A dermatoscopic image of a skin lesion:
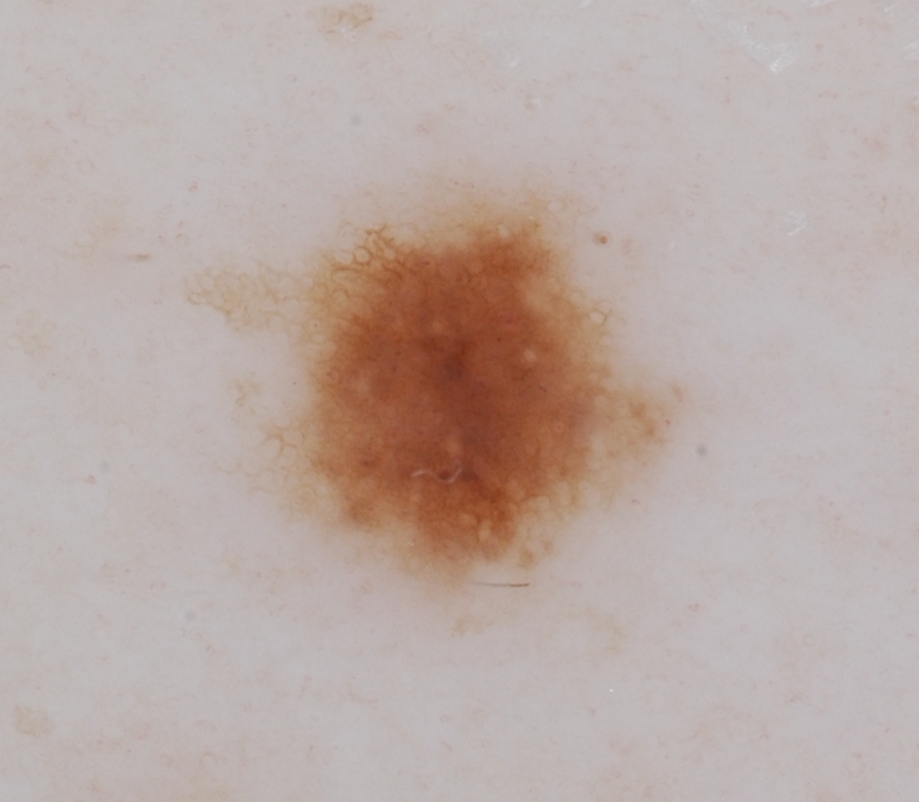location=(203, 178, 684, 602) | dermoscopic findings=globules and pigment network; absent: streaks, negative network, and milia-like cysts | assessment=a melanocytic nevus.